The photograph was taken at a distance · the lesion involves the arm — 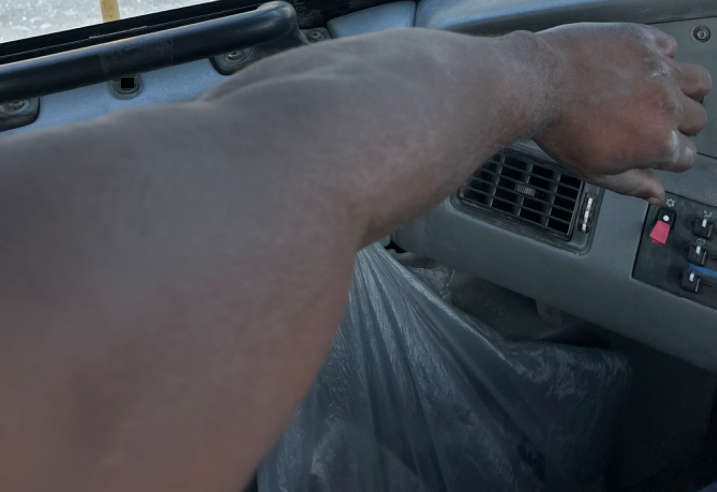Case summary:
- impression — consistent with Eczema